A female patient age 84:
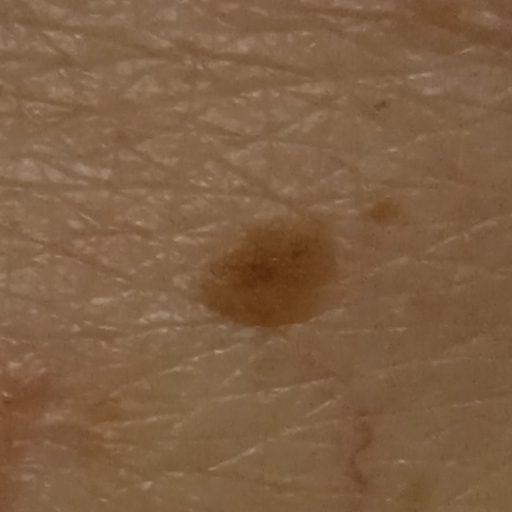The lesion measures approximately 5.9 mm.
Dermatologist review favored a seborrheic keratosis.